A dermoscopic close-up of a skin lesion — 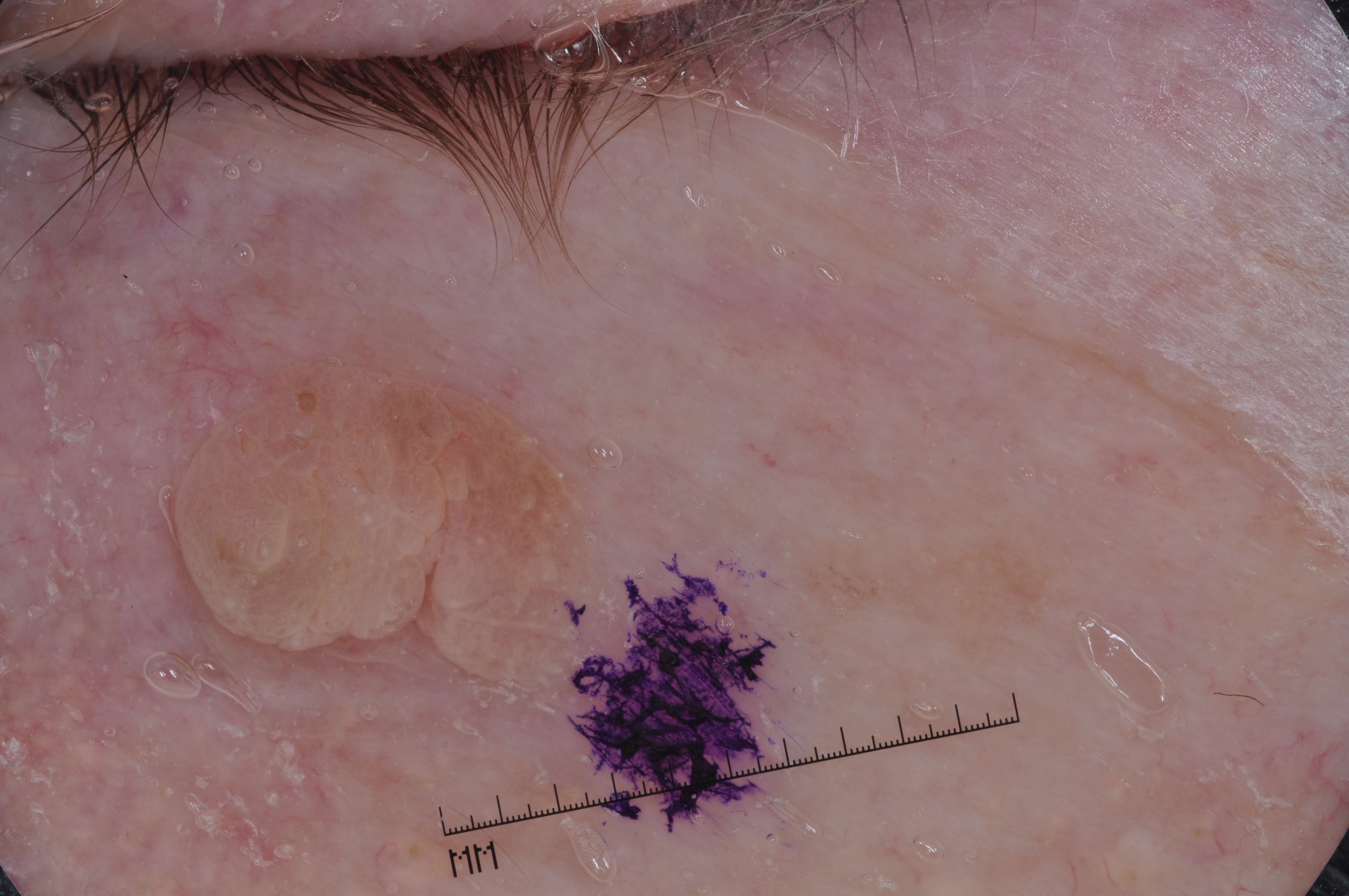Q: What is the lesion's bounding box?
A: 161, 349, 614, 707
Q: What does dermoscopy show?
A: milia-like cysts
Q: What is the diagnosis?
A: a seborrheic keratosis, a benign skin lesion